The photo was captured at an angle. Fitzpatrick phototype I: 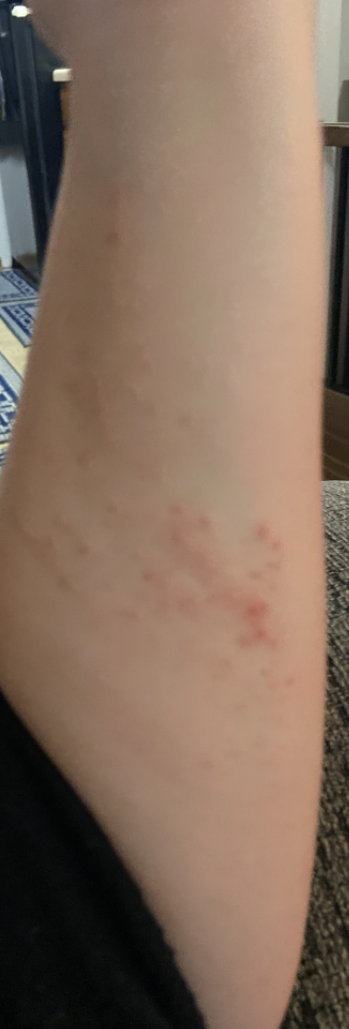Findings:
On teledermatology review, the impression is Allergic Contact Dermatitis.